The affected area is the leg · this is a close-up image — 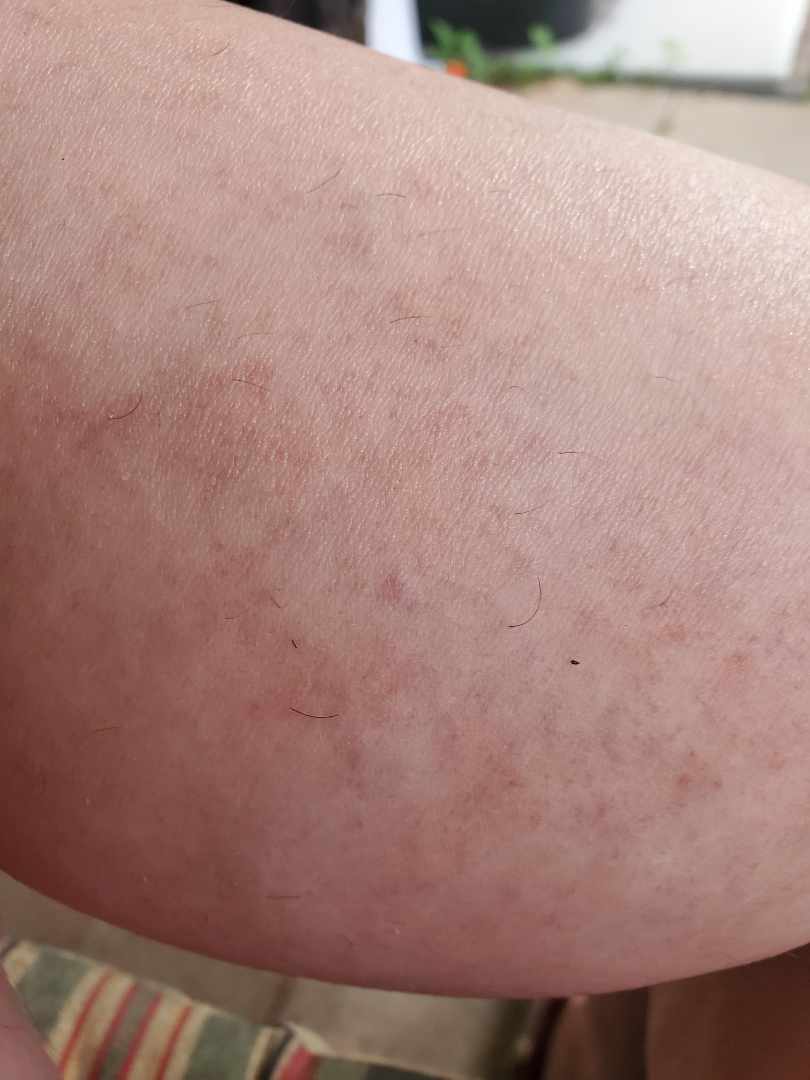Findings:
* assessment — unable to determine